Fitzpatrick IV, the patient considered this a rash, no associated systemic symptoms reported, close-up view, symptoms reported: enlargement:
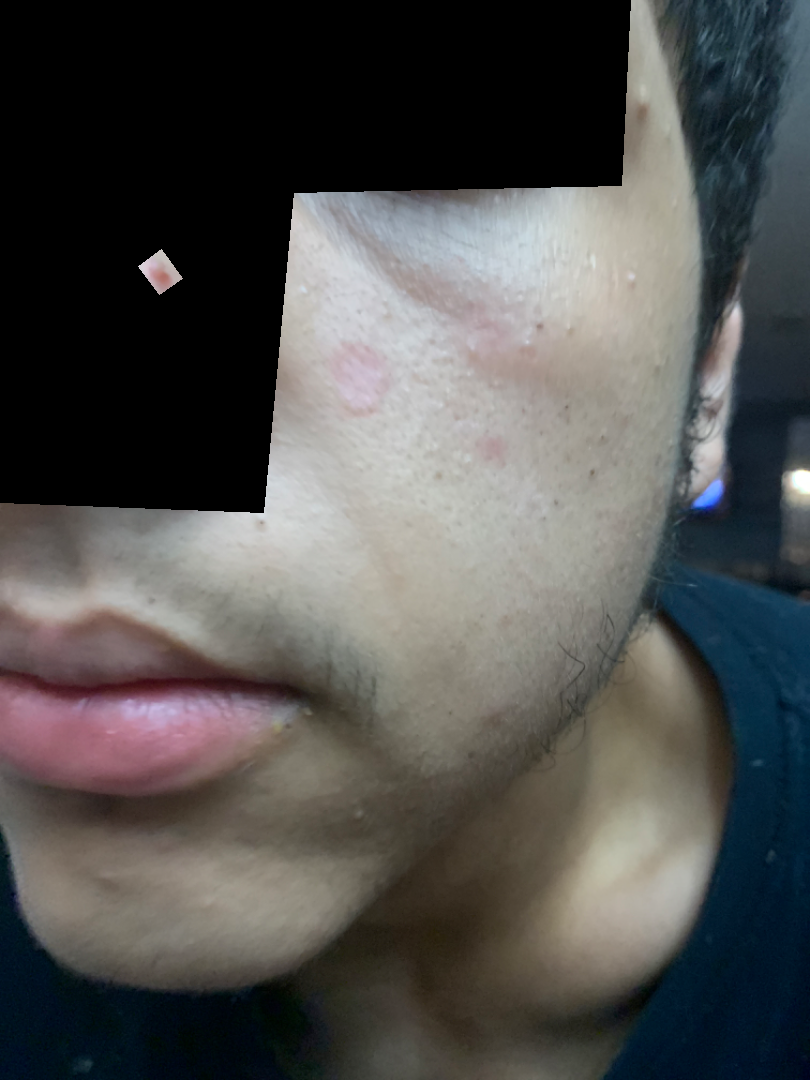Q: What is the dermatologist's impression?
A: Tinea (considered); Cutaneous lupus (considered); Seborrheic Dermatitis (considered)